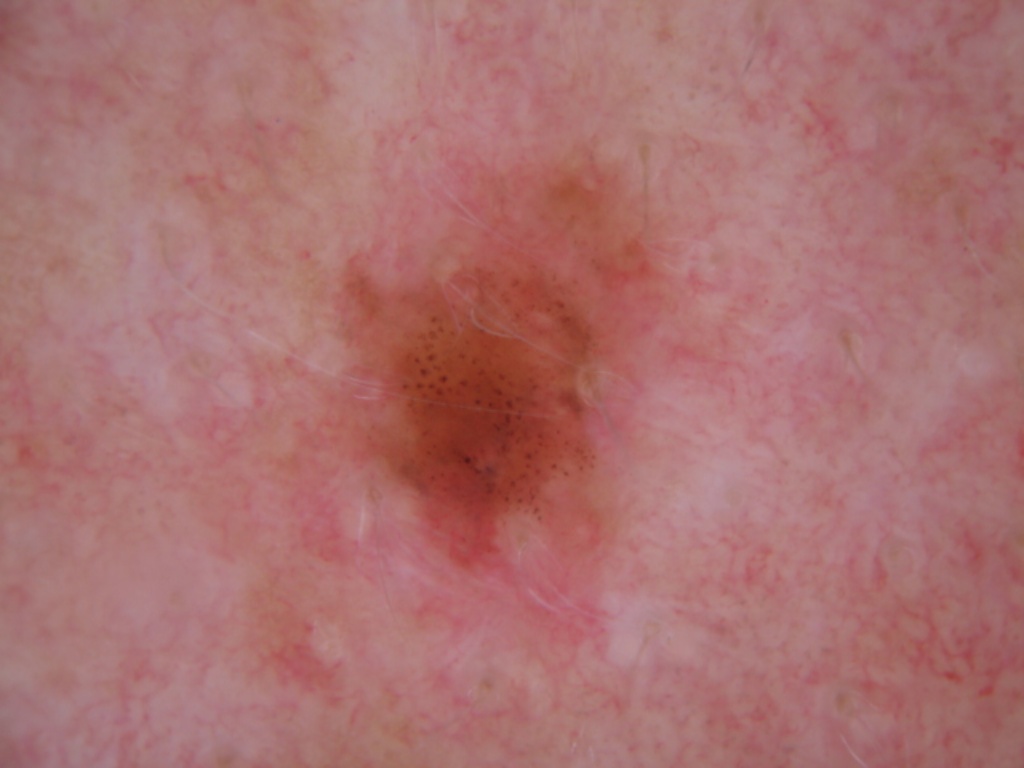modality = dermoscopic image; subject = male, aged approximately 45; lesion location = 344/168/653/568; dermoscopic features assessed but absent = globules, streaks, pigment network, negative network, and milia-like cysts; extent = ~9% of the field; assessment = a melanocytic nevus, a benign skin lesion.